The contributor notes the lesion is raised or bumpy · the photograph was taken at a distance · reported lesion symptoms include bothersome appearance, itching and burning · the condition has been present for less than one week · self-categorized by the patient as a rash:
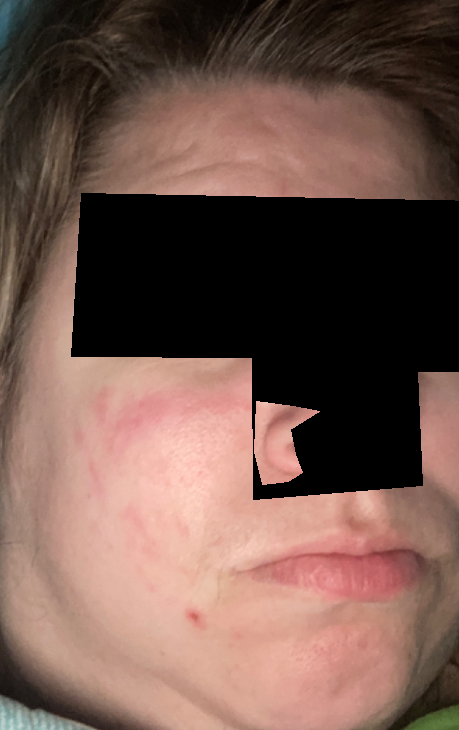Review:
On photographic review: Rosacea (0.54); Allergic Contact Dermatitis (0.23); Cutaneous lupus (0.23).